Recorded as Fitzpatrick phototype III · by history, prior malignancy (patient or family), tobacco use, and alcohol use · a clinical photograph of a skin lesion:
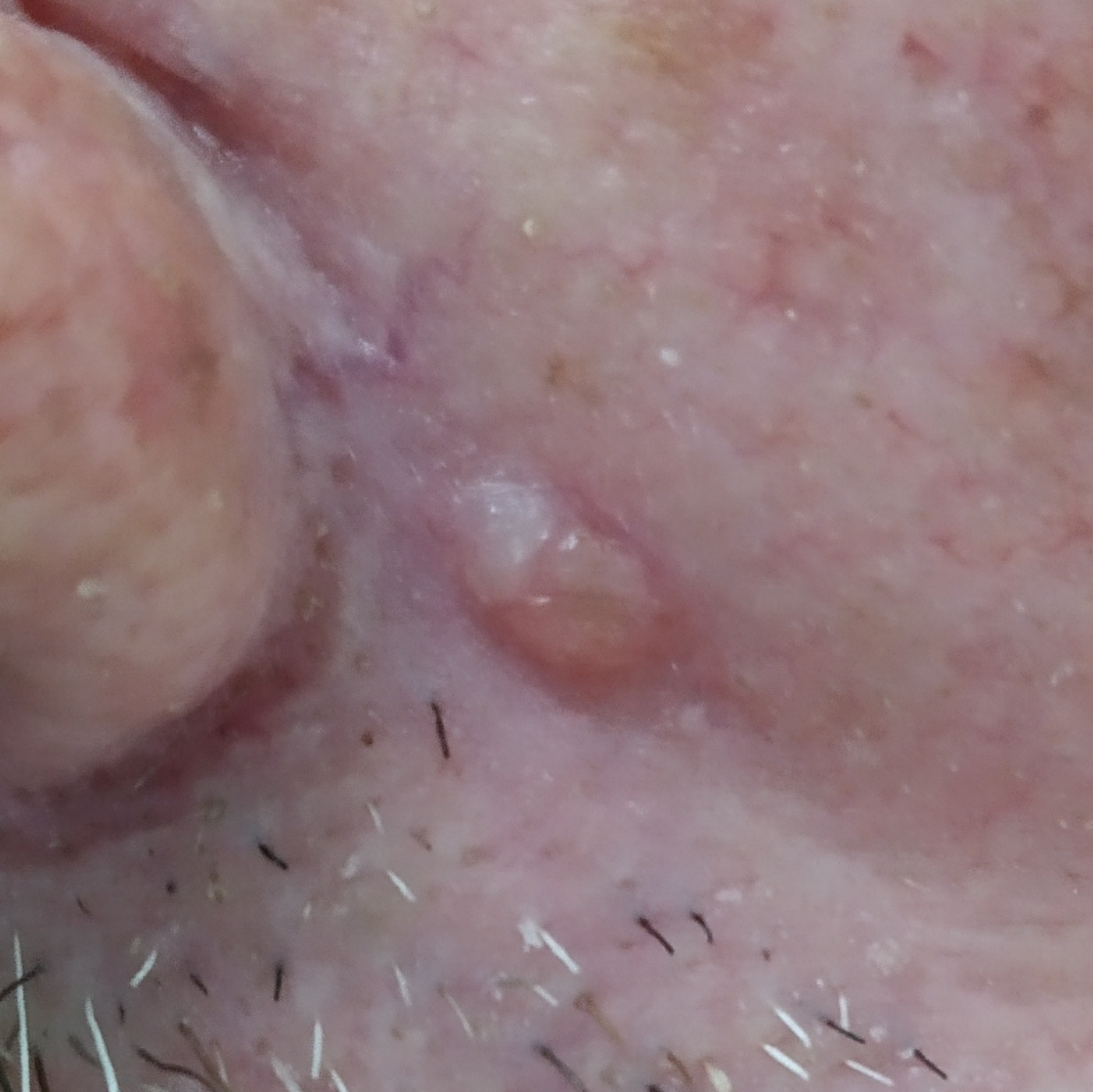The lesion involves the face.
Measuring about 6 × 3 mm.
The patient describes that the lesion itches and is elevated, but does not hurt.
On biopsy, the diagnosis was a malignancy — a basal cell carcinoma.